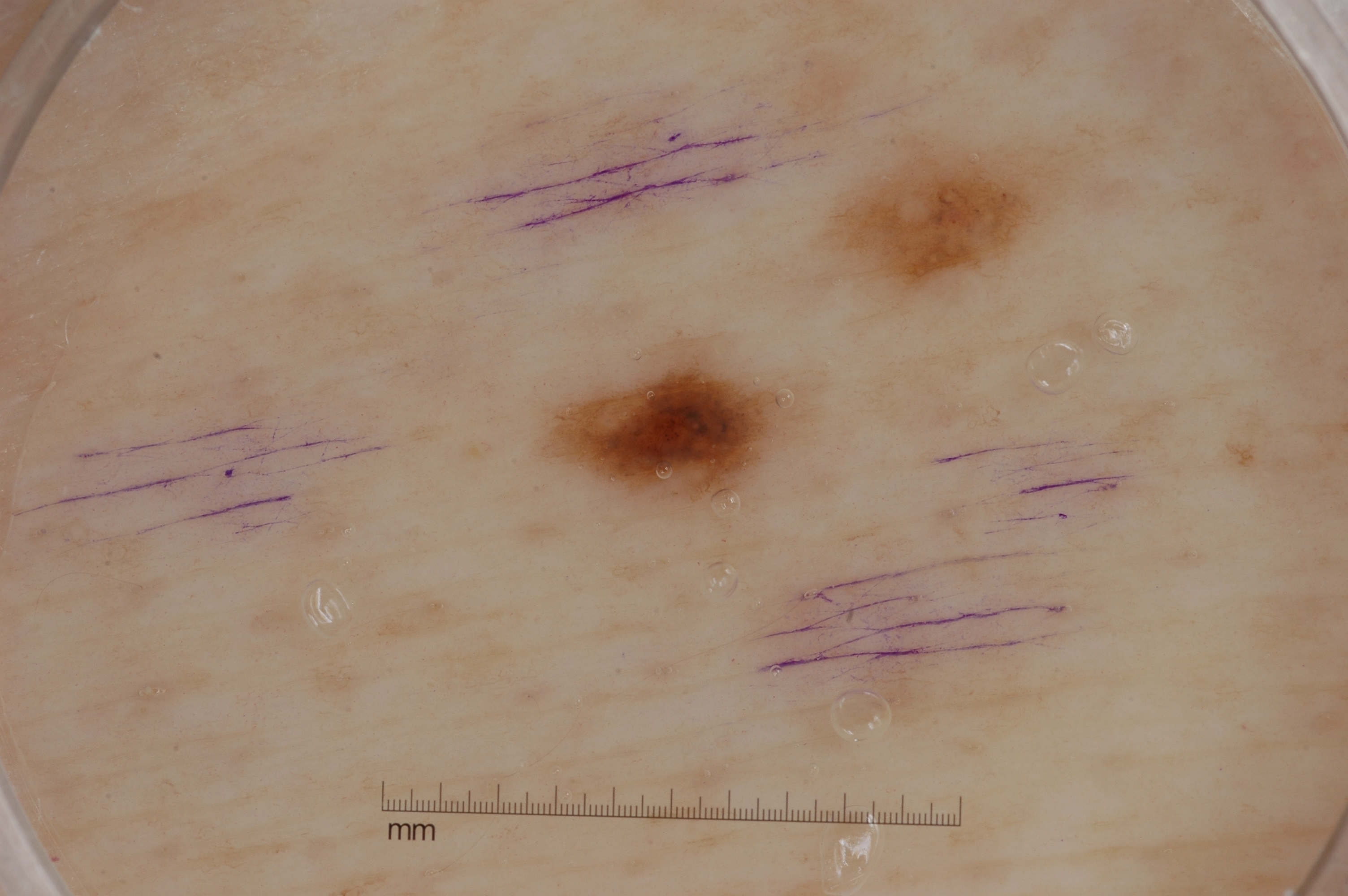Case summary: A dermatoscopic image of a skin lesion. The lesion is small relative to the field of view. Dermoscopic review identifies no streaks, negative network, pigment network, or milia-like cysts. With coordinates (x1, y1, x2, y2), the lesion is bounded by <box>548, 350, 789, 503</box>. Assessment: Consistent with a melanocytic nevus, a benign skin lesion.